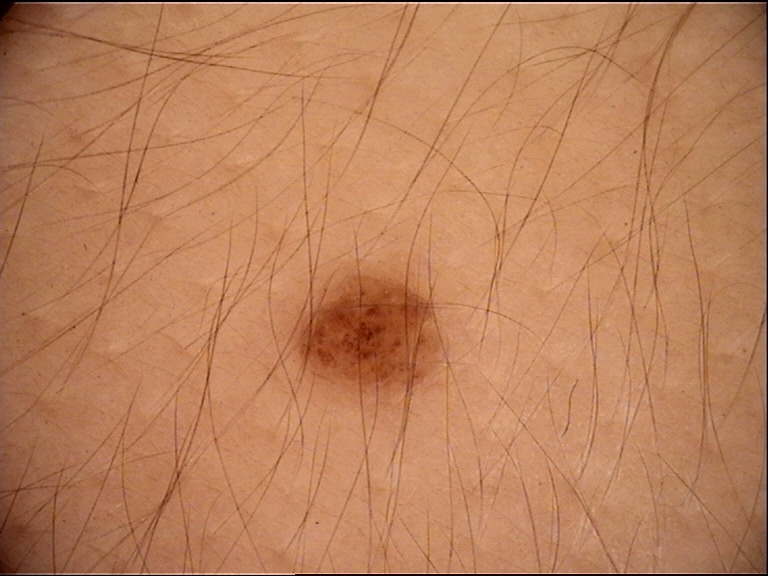modality: dermoscopy | subtype: banal | label: compound nevus (expert consensus).